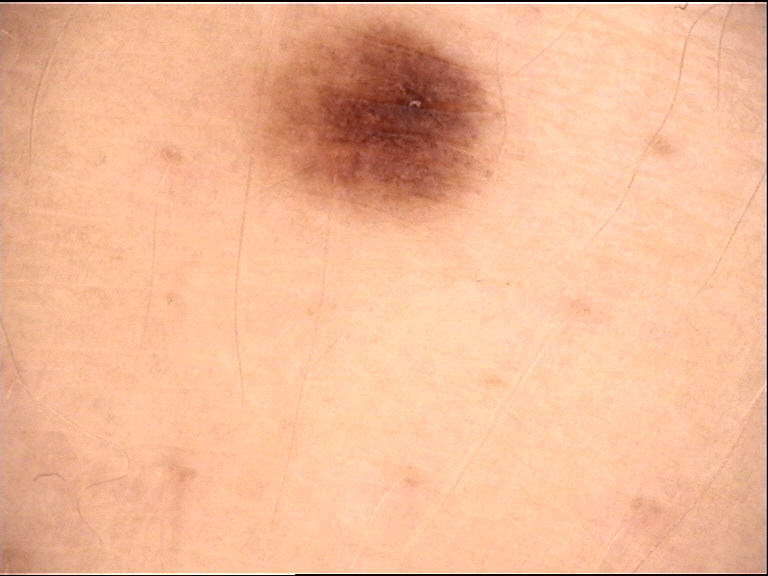A dermoscopic image of a skin lesion.
The diagnosis was a dysplastic junctional nevus.